A dermoscopic image of a skin lesion: 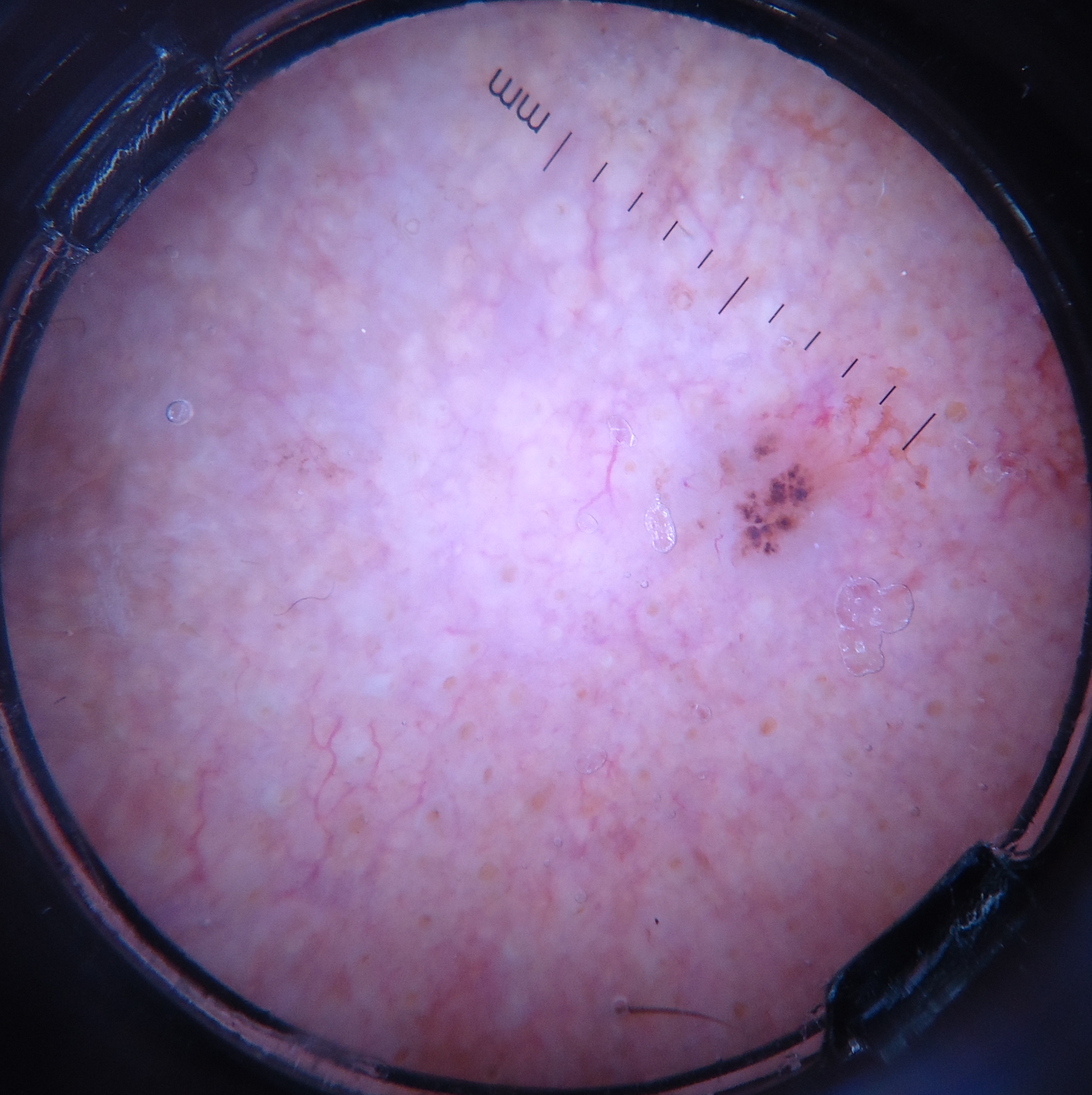label: basal cell carcinoma (biopsy-proven).